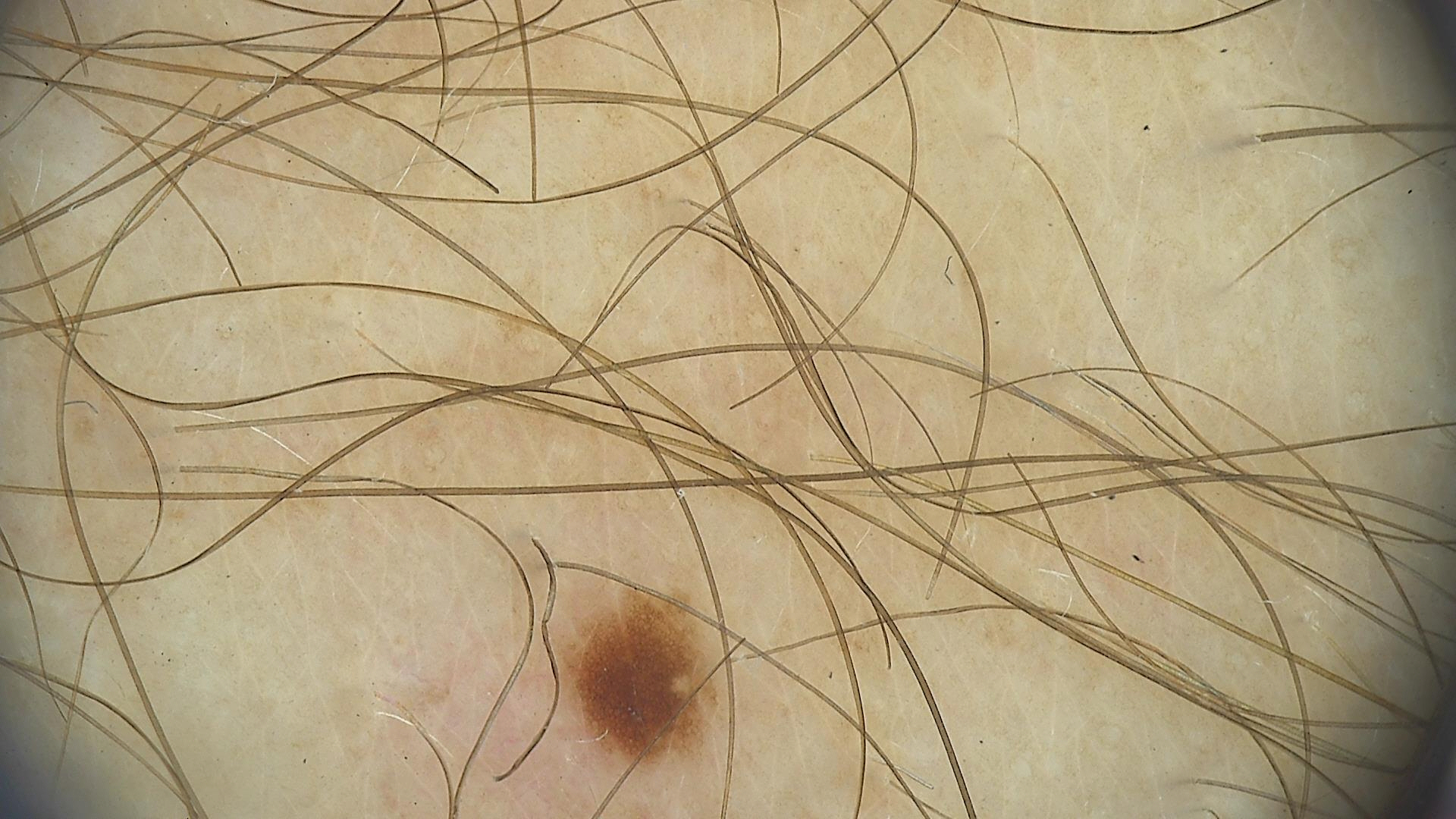diagnostic label: dysplastic junctional nevus (expert consensus).